A dermoscopic photograph of a skin lesion.
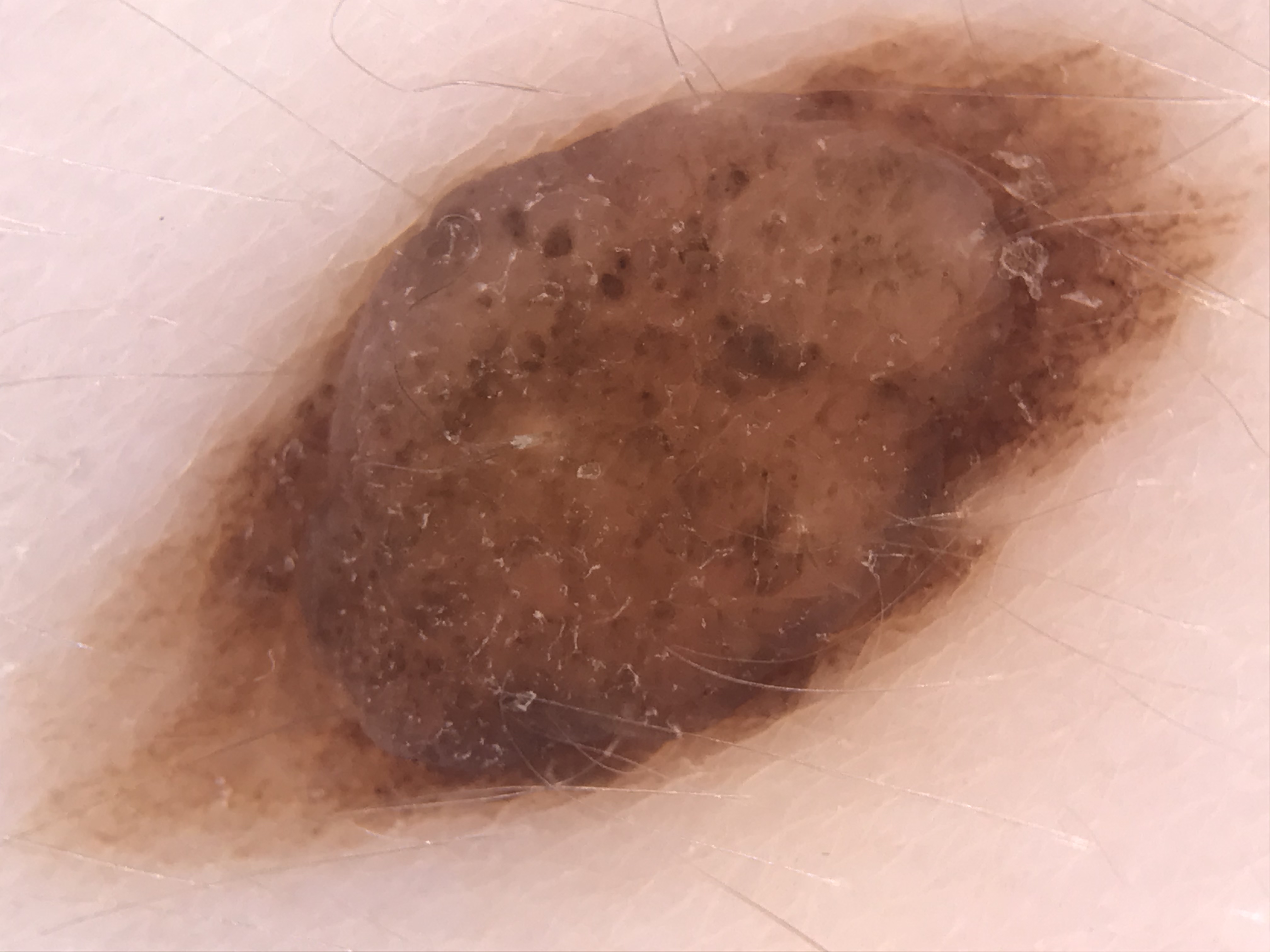Consistent with a dysplastic compound nevus.